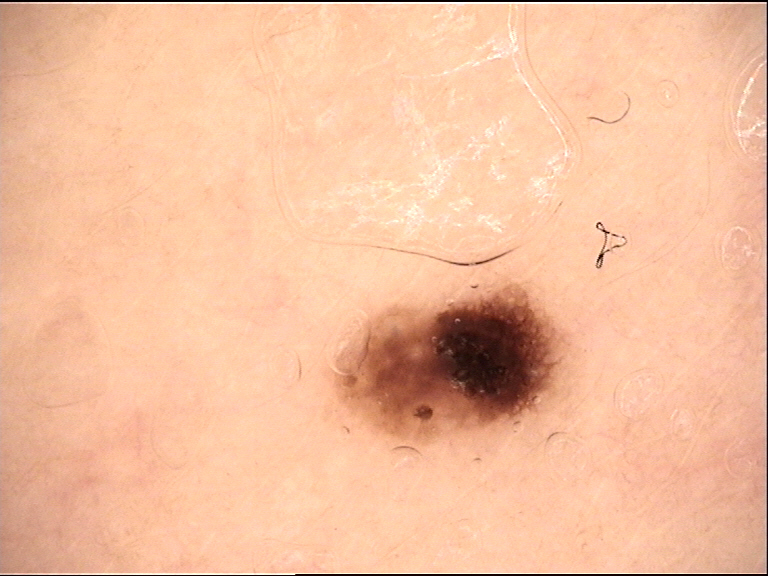The diagnosis was a dysplastic junctional nevus.